A female subject aged approximately 30. This is a dermoscopic photograph of a skin lesion — 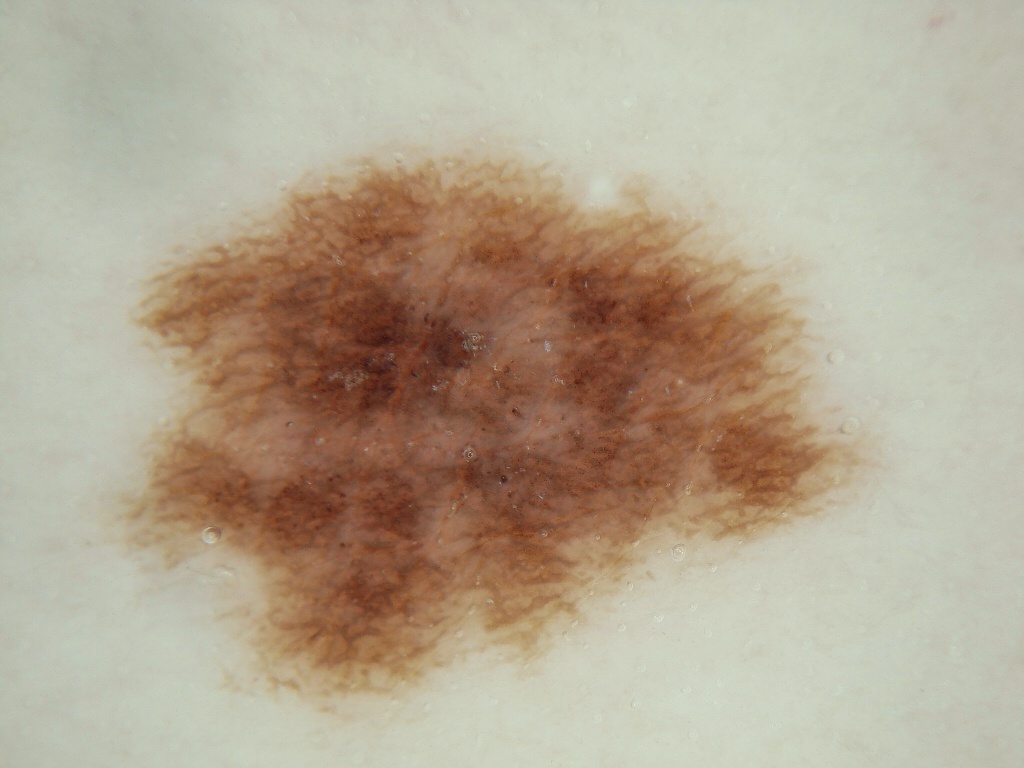The lesion takes up a large portion of the image. Dermoscopy demonstrates milia-like cysts and pigment network, with no negative network, streaks, or globules. As (left, top, right, bottom), the lesion occupies the region [87, 141, 875, 714]. Expert review diagnosed this as a melanocytic nevus.